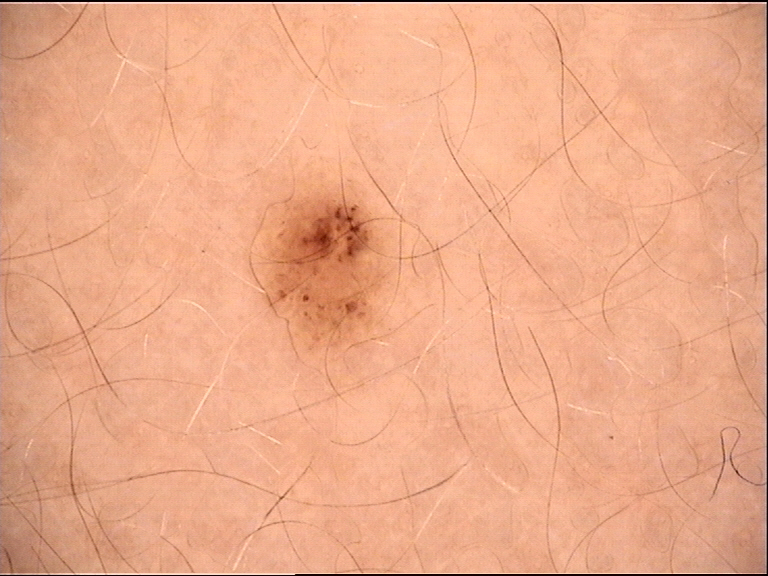Conclusion:
The diagnosis was a banal lesion — a junctional nevus.